Skin tone: Fitzpatrick skin type III · the arm is involved · the patient notes itching and bothersome appearance · self-categorized by the patient as a rash · the contributor is 50–59, female · the photograph is a close-up of the affected area · the lesion is described as raised or bumpy · the condition has been present for more than one year: 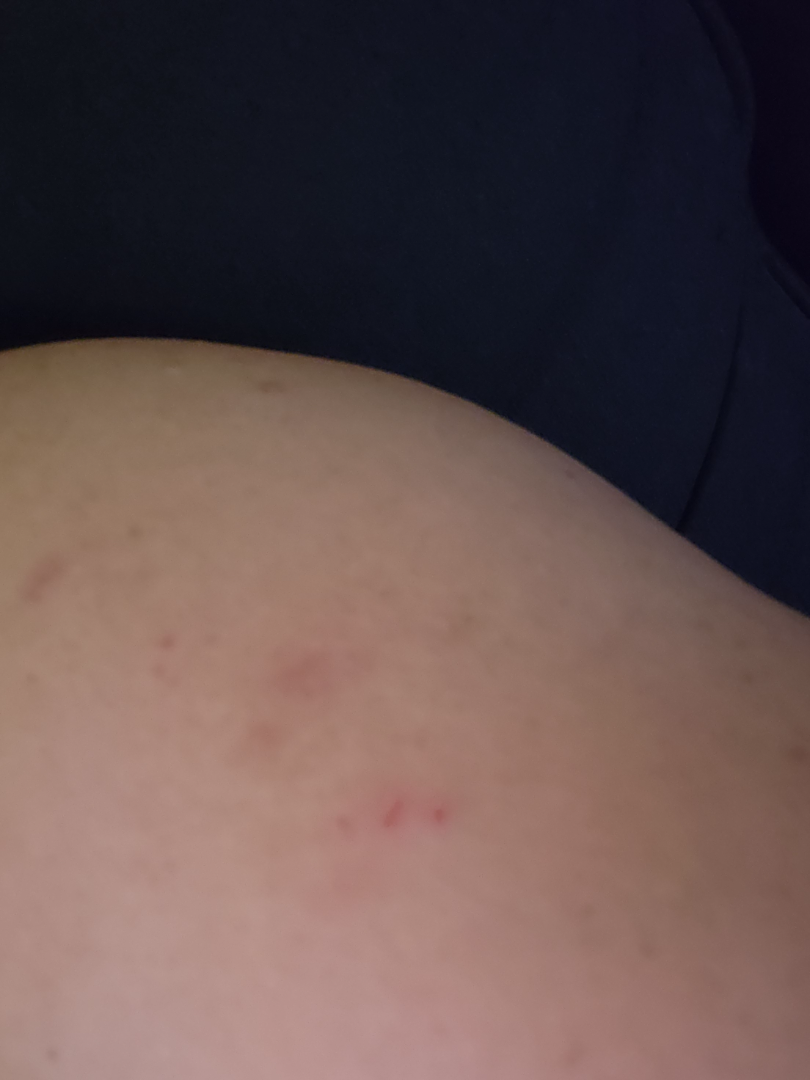Findings:
* assessment — indeterminate